A male subject 39 years old; a clinical photograph of a skin lesion; Fitzpatrick II:
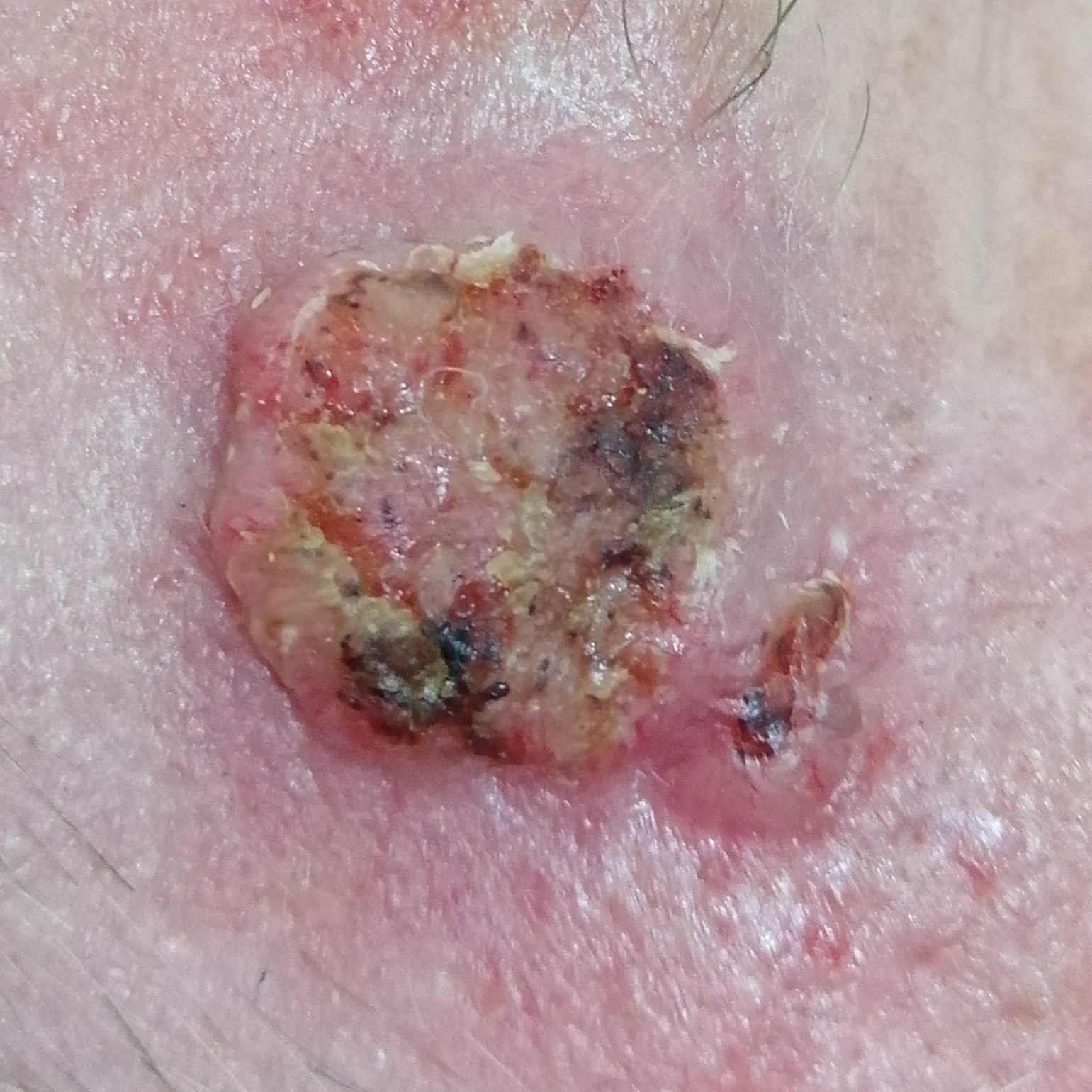The lesion is on the face. The lesion is roughly 20 by 14 mm. Biopsy-confirmed as a skin cancer — a basal cell carcinoma.